A skin lesion imaged with a dermatoscope.
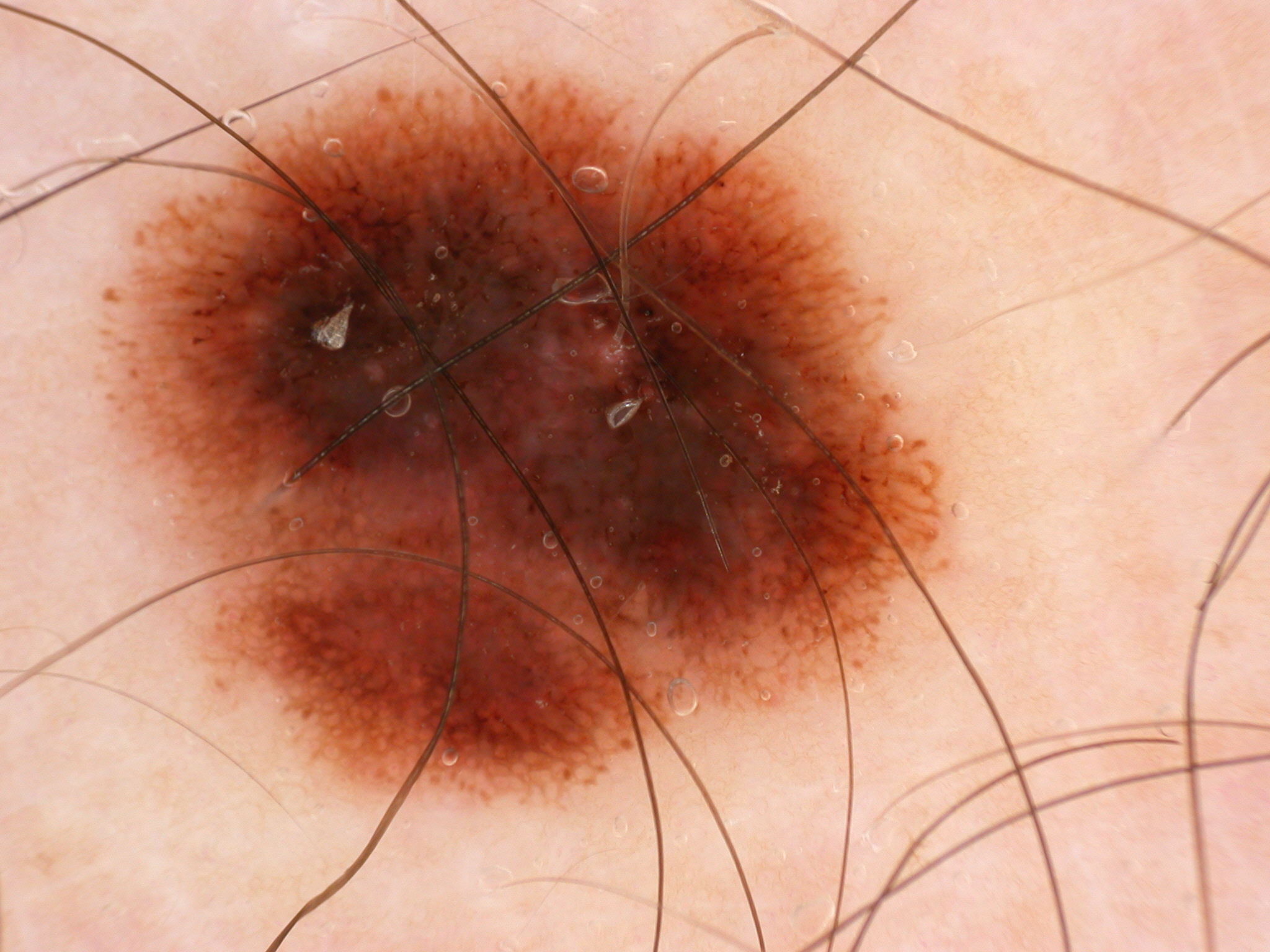The lesion takes up a large portion of the image. Dermoscopy demonstrates pigment network, globules, and streaks; no negative network or milia-like cysts. As (left, top, right, bottom), the lesion's extent is [84,72,955,814]. The clinical diagnosis was a melanocytic nevus.